Dermoscopy of a skin lesion — 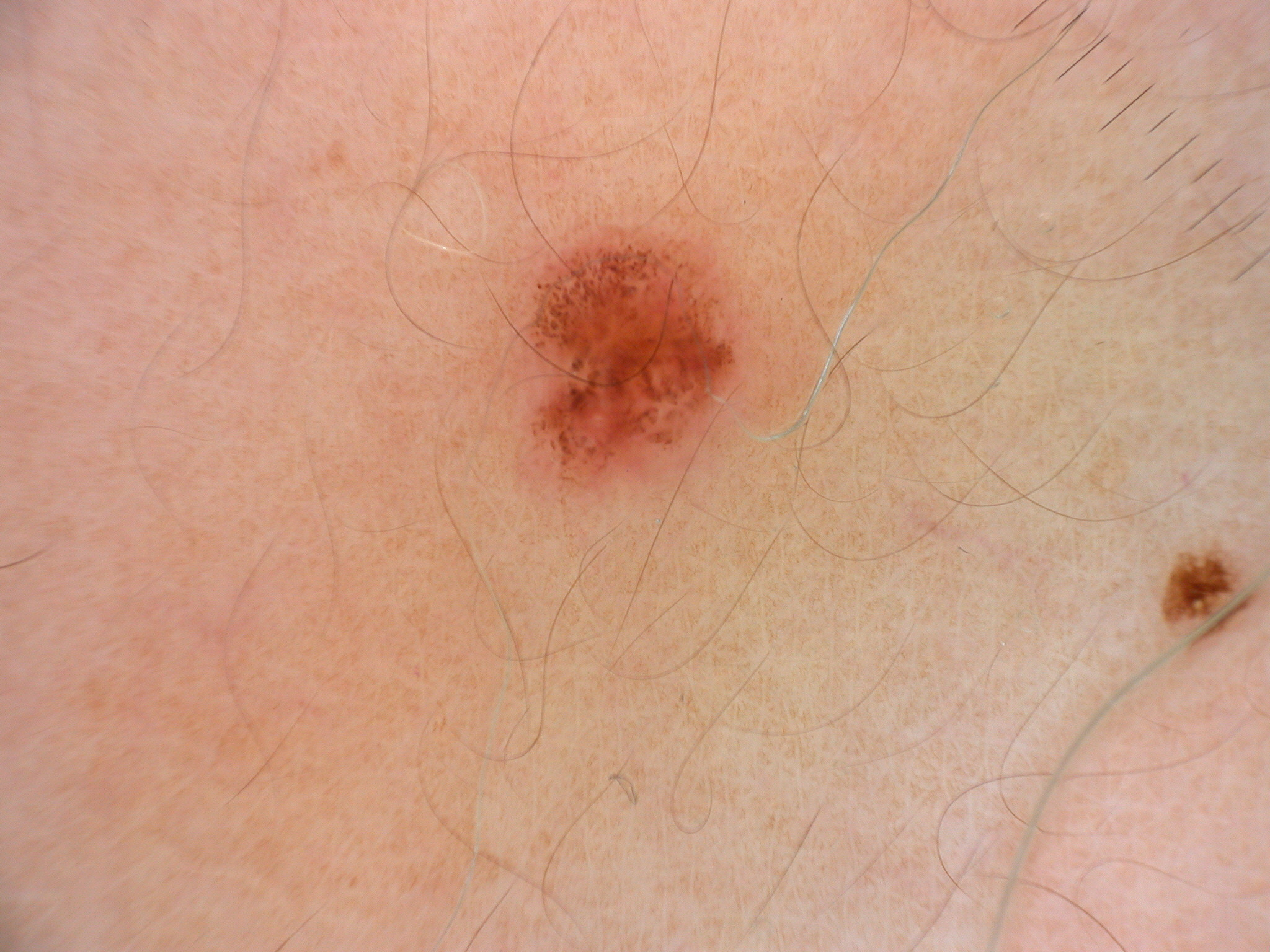Q: What is the lesion's bounding box?
A: x1=521, y1=229, x2=747, y2=488
Q: Which dermoscopic features are absent?
A: globules, negative network, pigment network, milia-like cysts, and streaks
Q: What is the diagnosis?
A: a melanocytic nevus